A dermoscopic close-up of a skin lesion.
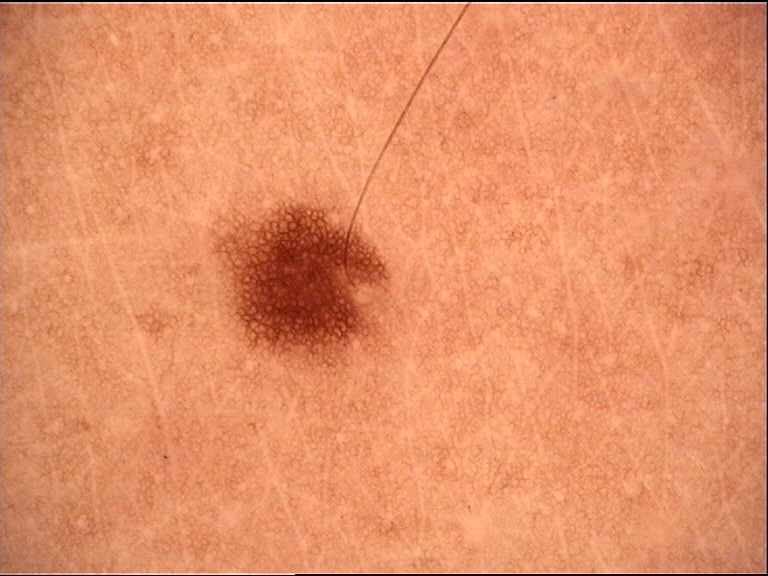Classified as a junctional nevus.